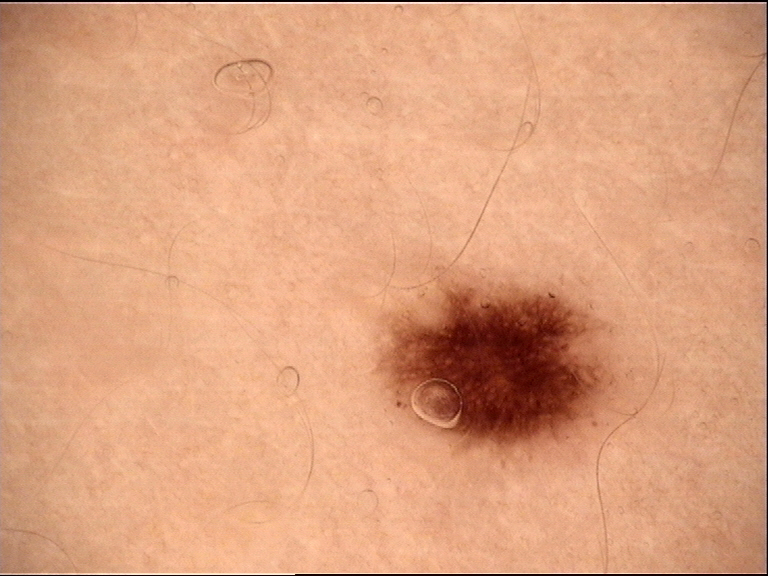Consistent with a dysplastic junctional nevus.